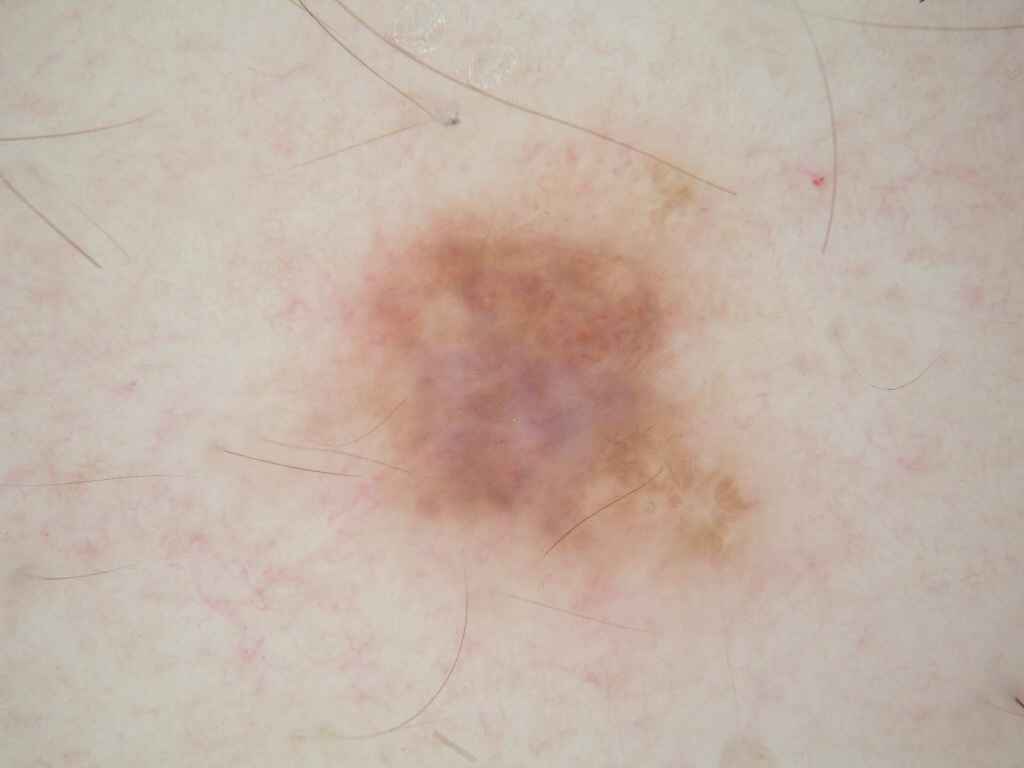Image and clinical context:
A dermoscopy image of a single skin lesion. In (x1, y1, x2, y2) order, the lesion occupies the region (293, 130, 787, 604).
Assessment:
Clinically diagnosed as a melanocytic nevus.